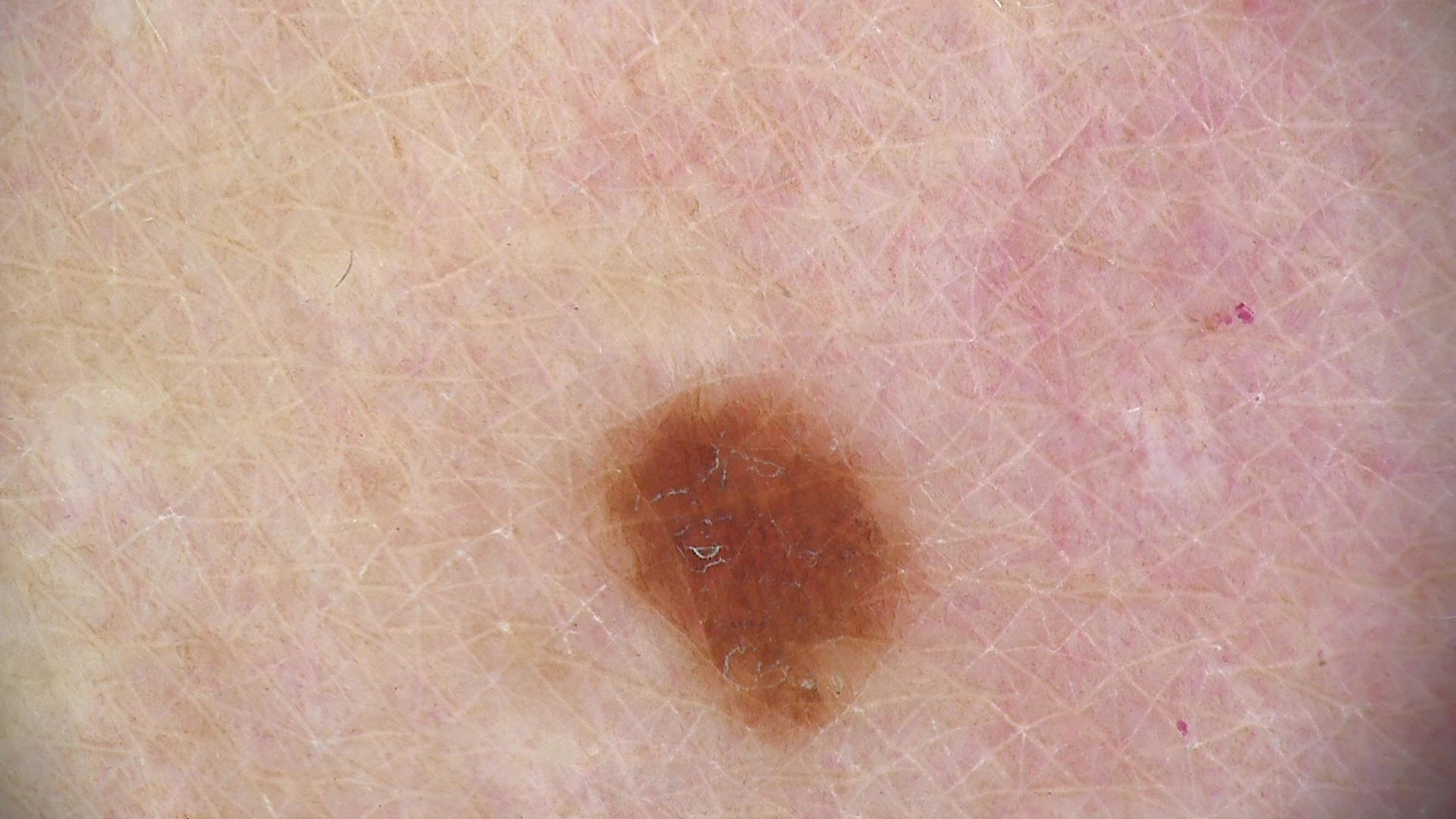Q: What is this lesion?
A: junctional nevus (expert consensus)